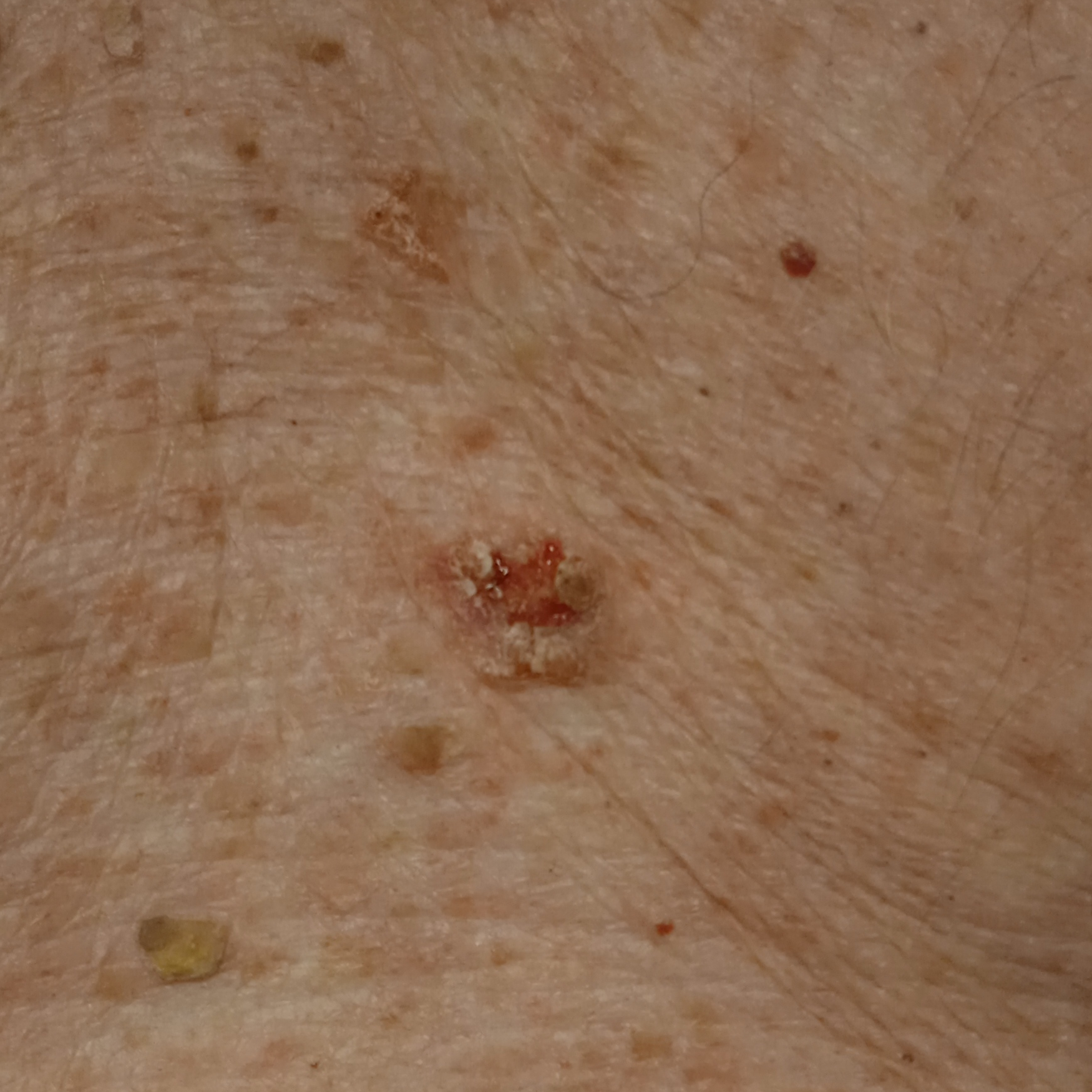Clinical context:
The patient says their skin reddens with sun exposure. The referring clinician suspected Bowen's disease. A male subject 83 years old. A clinical photograph showing a skin lesion. The lesion is on the torso. Measuring roughly 14.5 mm.
Impression:
The consensus diagnosis for this lesion was a squamous cell carcinoma.